A skin lesion imaged with a dermatoscope.
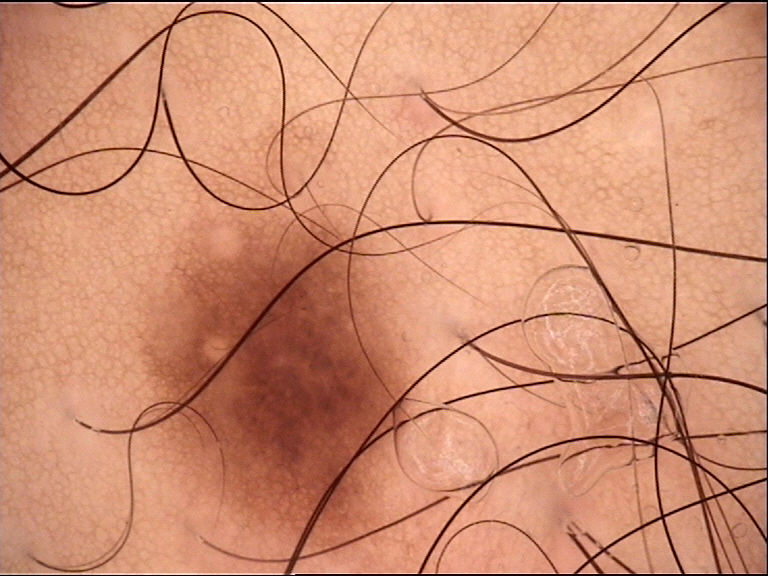Diagnosed as a dysplastic junctional nevus.